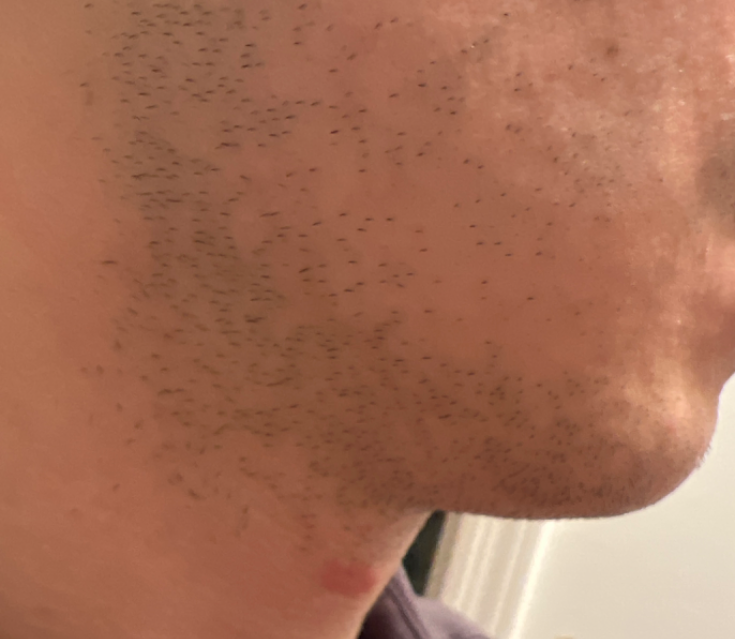Impression: One reviewing dermatologist: Skin and soft tissue atypical mycobacterial infection and Basal Cell Carcinoma were considered with similar weight; a more distant consideration is Pityriasis rosea.